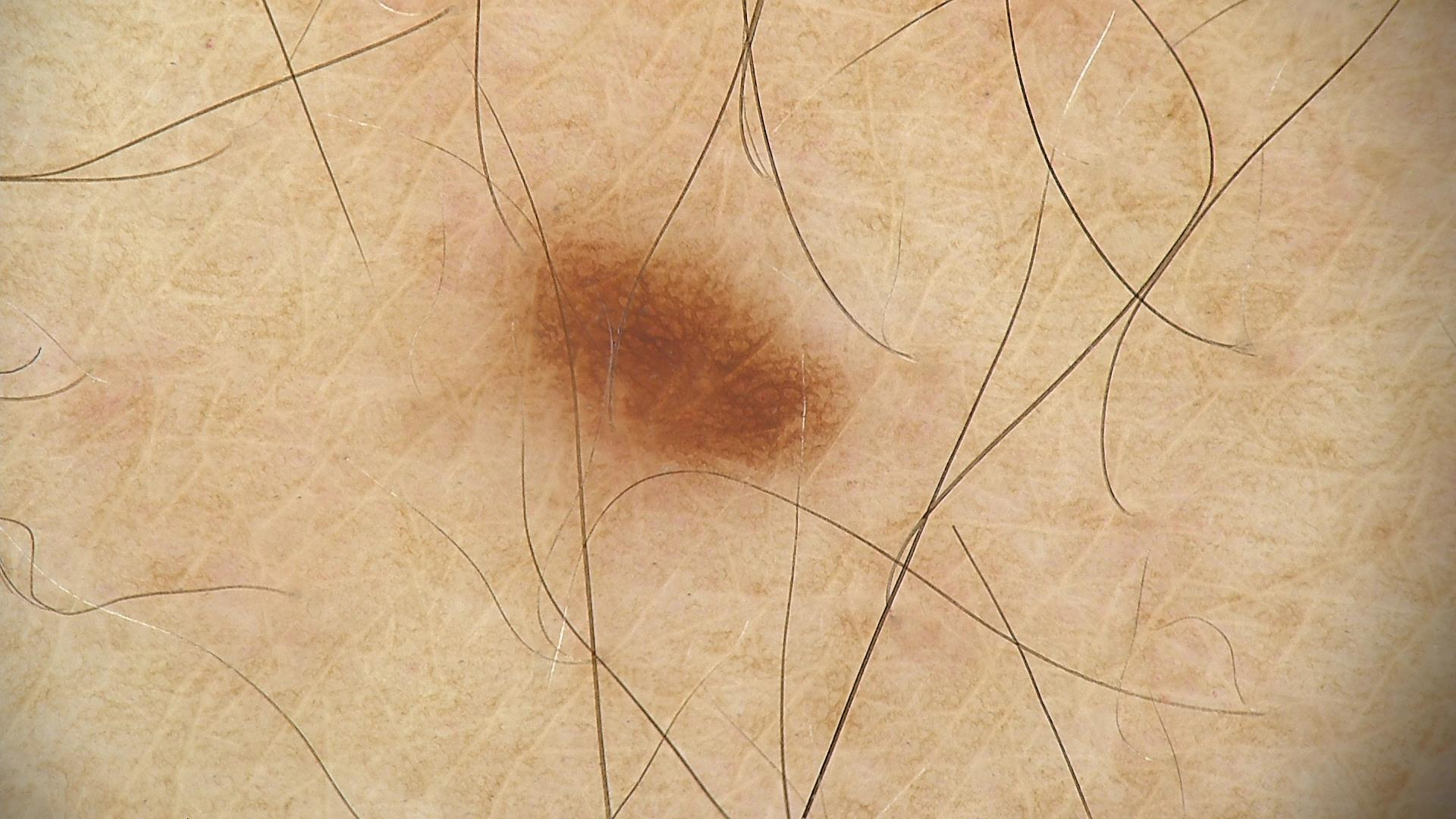image: dermatoscopy
diagnosis:
  name: dysplastic junctional nevus
  code: jd
  malignancy: benign
  super_class: melanocytic
  confirmation: expert consensus